A dermatoscopic image of a skin lesion.
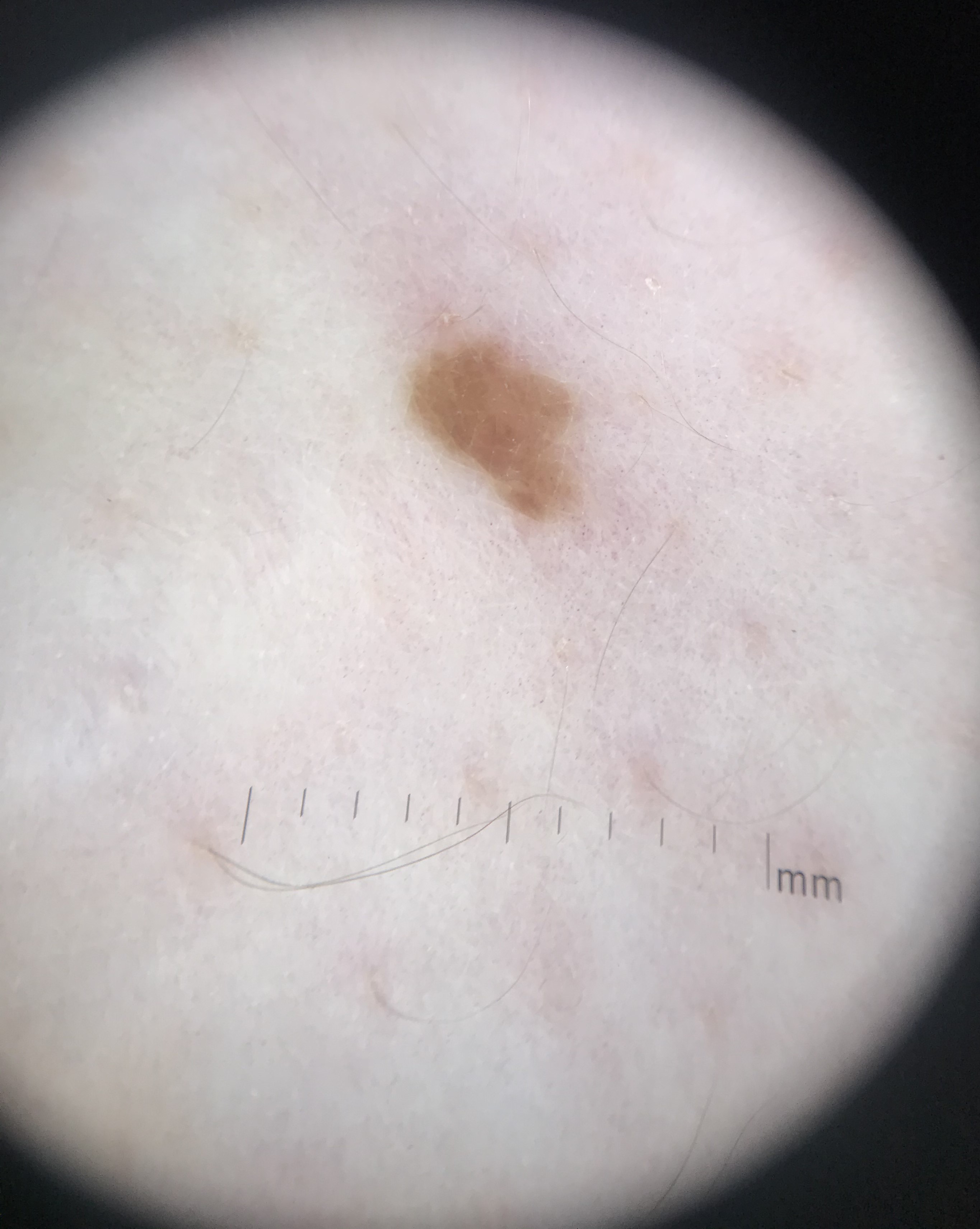Labeled as a keratinocytic, benign lesion — a seborrheic keratosis.